The lesion involves the arm and leg · the patient described the issue as a rash · texture is reported as raised or bumpy · associated systemic symptoms include joint pain · the patient did not report lesion symptoms · the photo was captured at an angle.
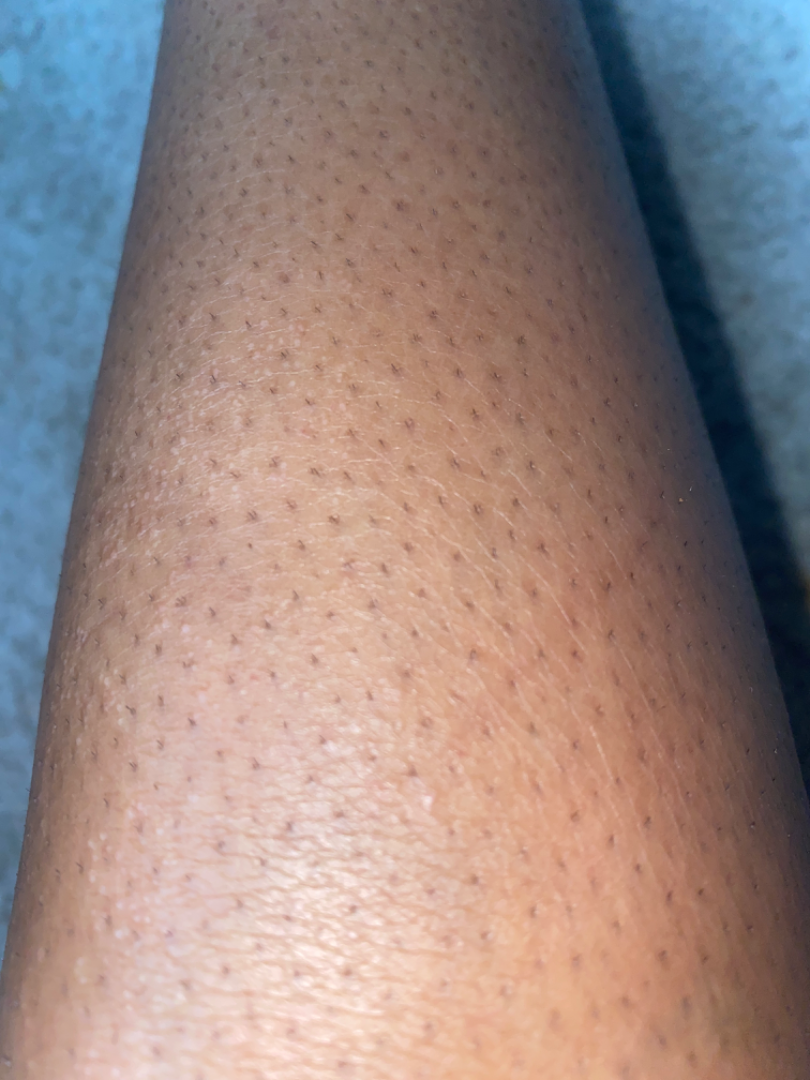differential:
  Eczema: 0.5
  Xerosis: 0.5